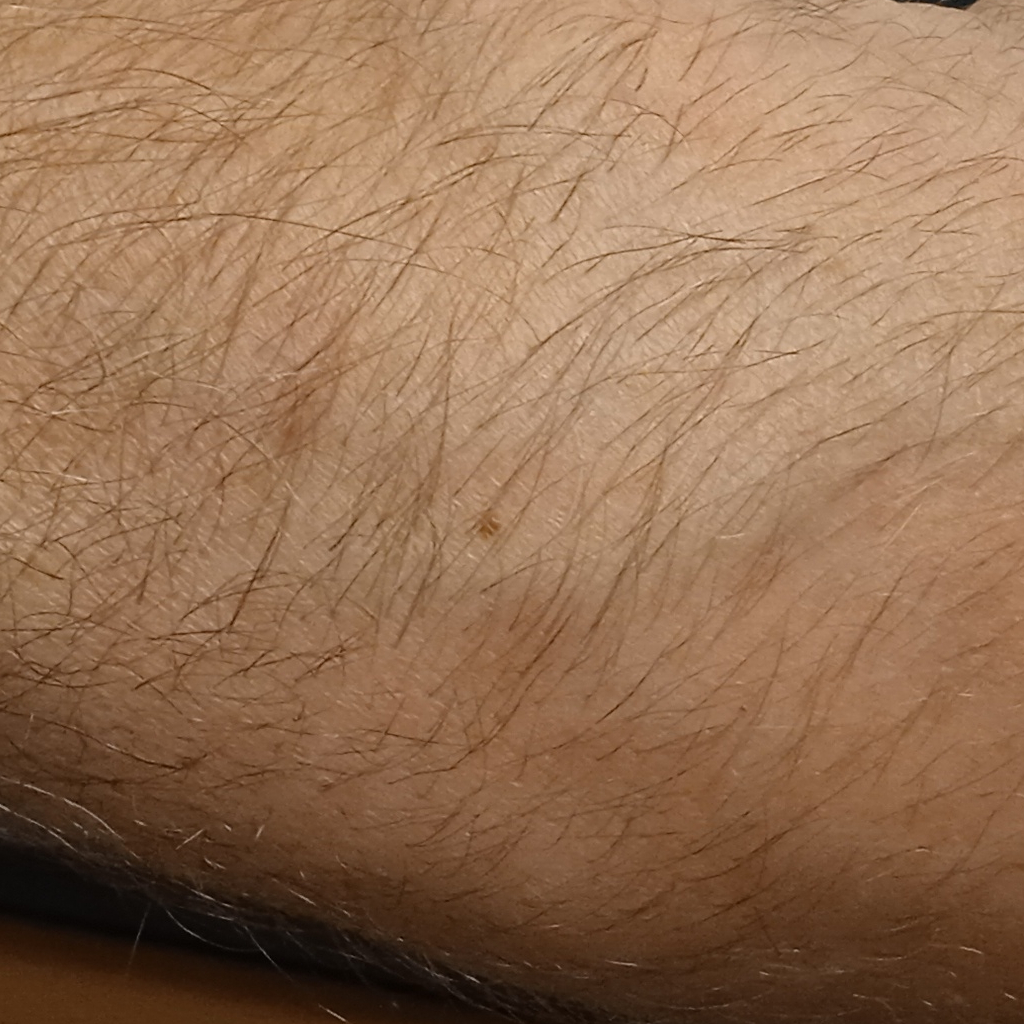Impression:
Dermatologist review favored a melanocytic nevus.